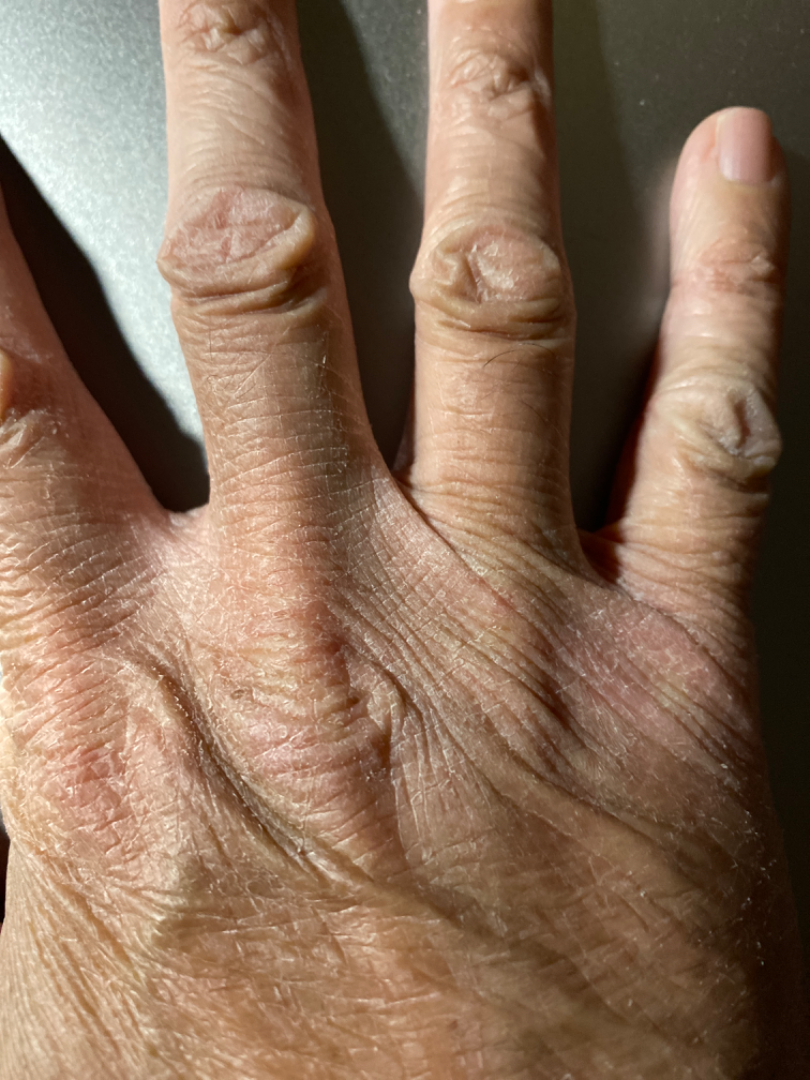On remote review of the image: Eczema (possible); Xerosis (possible); Tinea (possible).